Dermoscopy of a skin lesion — 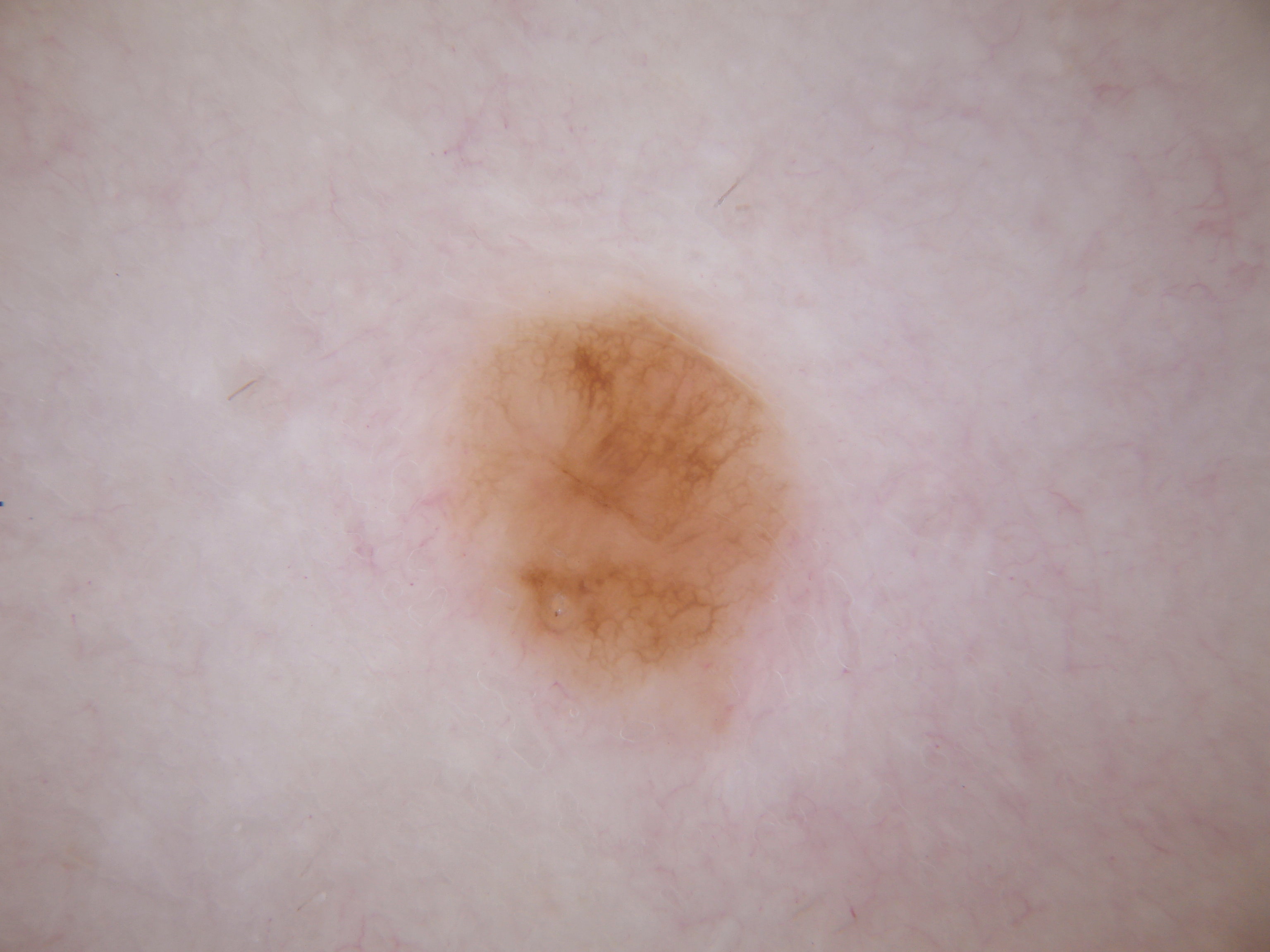Q: How much of the field does the lesion occupy?
A: ~10% of the field
Q: Which dermoscopic features were noted?
A: pigment network; absent: streaks, negative network, milia-like cysts, and globules
Q: Where is the lesion located?
A: 432/293/800/709
Q: What is the diagnosis?
A: a melanocytic nevus